The photograph was taken at a distance — 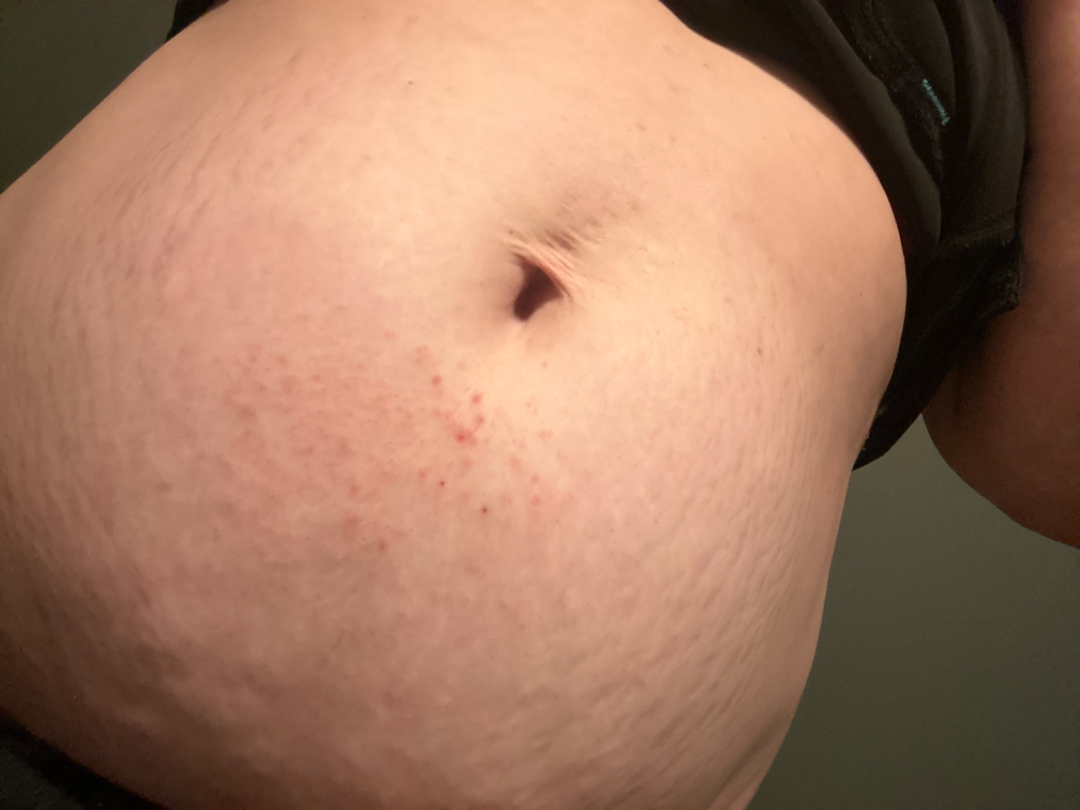On remote dermatologist review: favoring Eczema; also consider Pemphigoid gestationis; the differential also includes Pruritic urticarial papules and plaques of pregnancy.